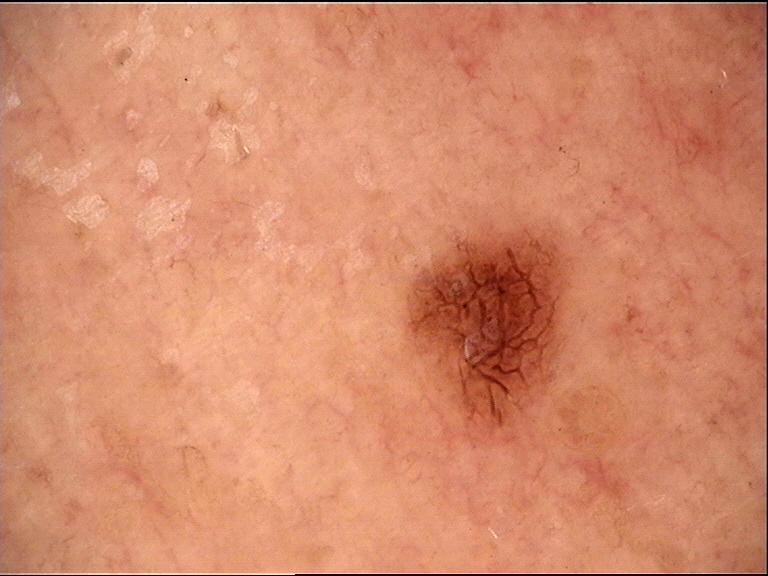{"image": "dermoscopy", "diagnosis": {"name": "dysplastic junctional nevus", "code": "jd", "malignancy": "benign", "super_class": "melanocytic", "confirmation": "expert consensus"}}